A male patient aged 43-47; this is a dermoscopic photograph of a skin lesion.
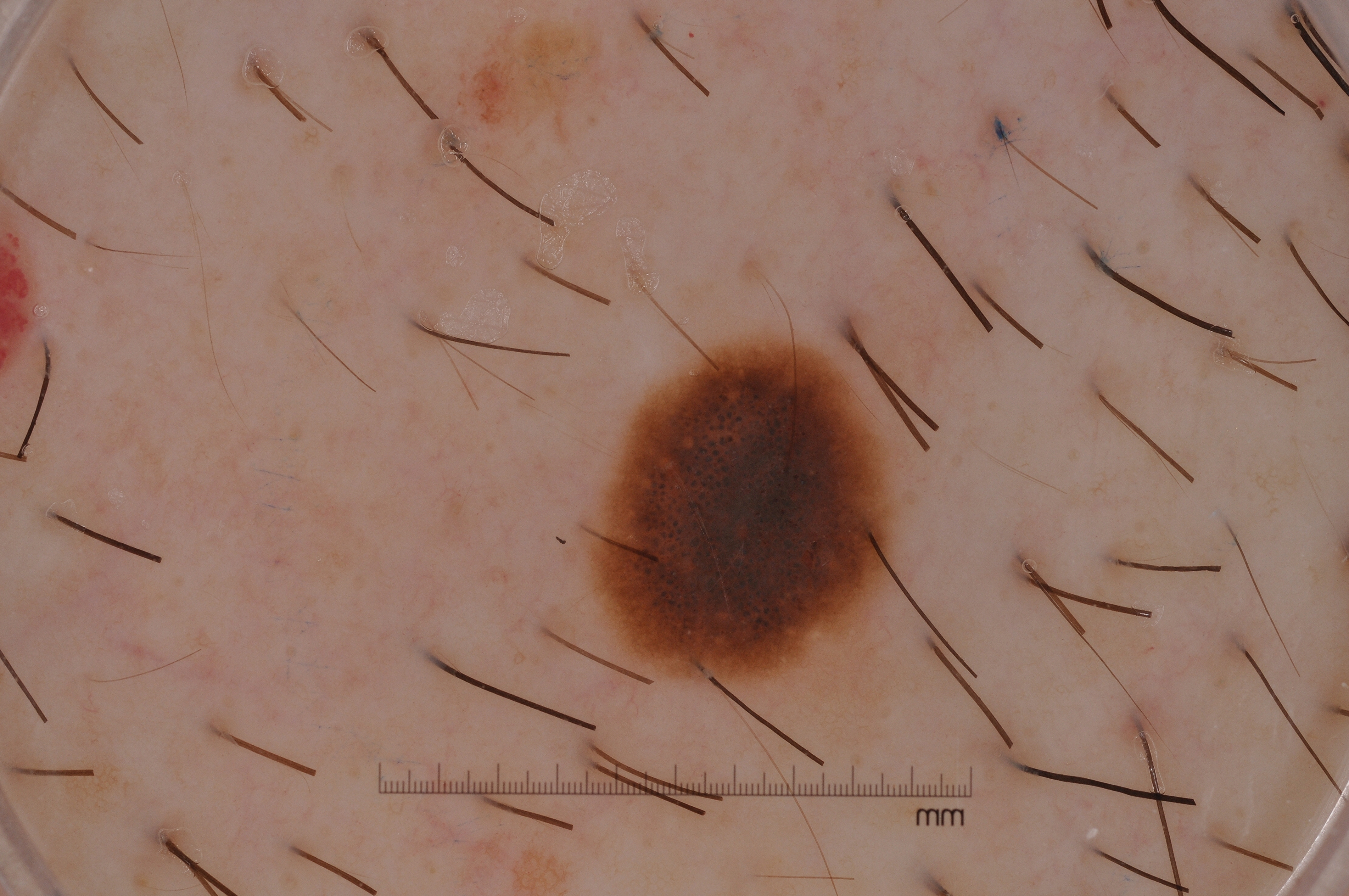Case summary:
In (x1, y1, x2, y2) order, the lesion spans (590, 337, 896, 686). Dermoscopically, the lesion shows no pigment network, negative network, streaks, or milia-like cysts.
Impression:
The clinical diagnosis was a melanocytic nevus, a benign skin lesion.